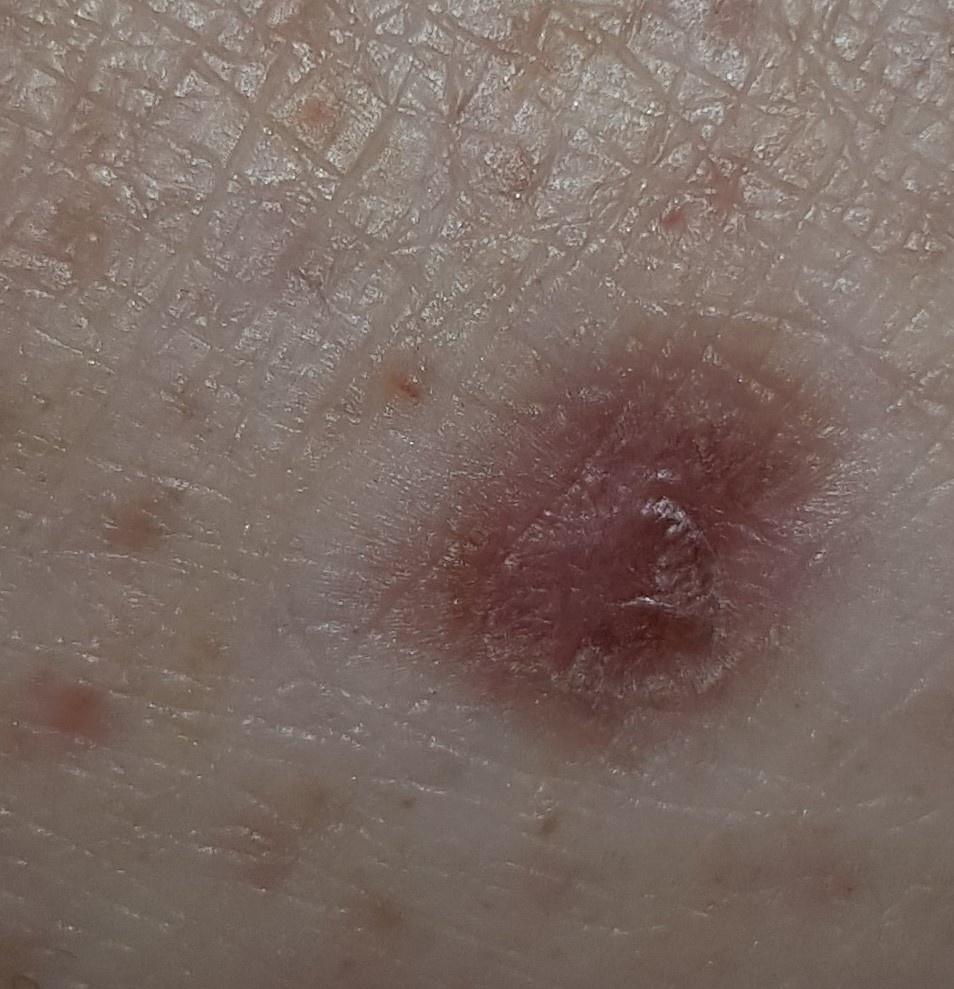| key | value |
|---|---|
| patient | male, aged approximately 60 |
| location | a lower extremity |
| diagnosis | Dermatofibroma (biopsy-proven) |